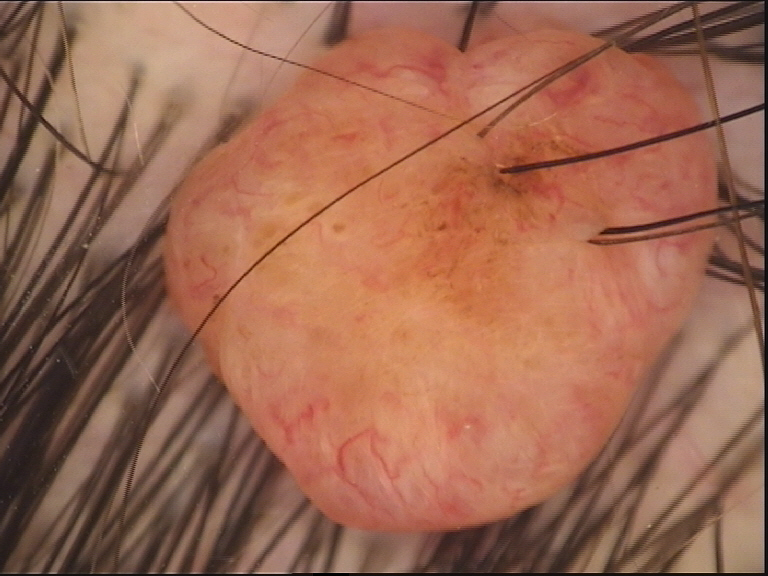Impression: Labeled as a dermal nevus.